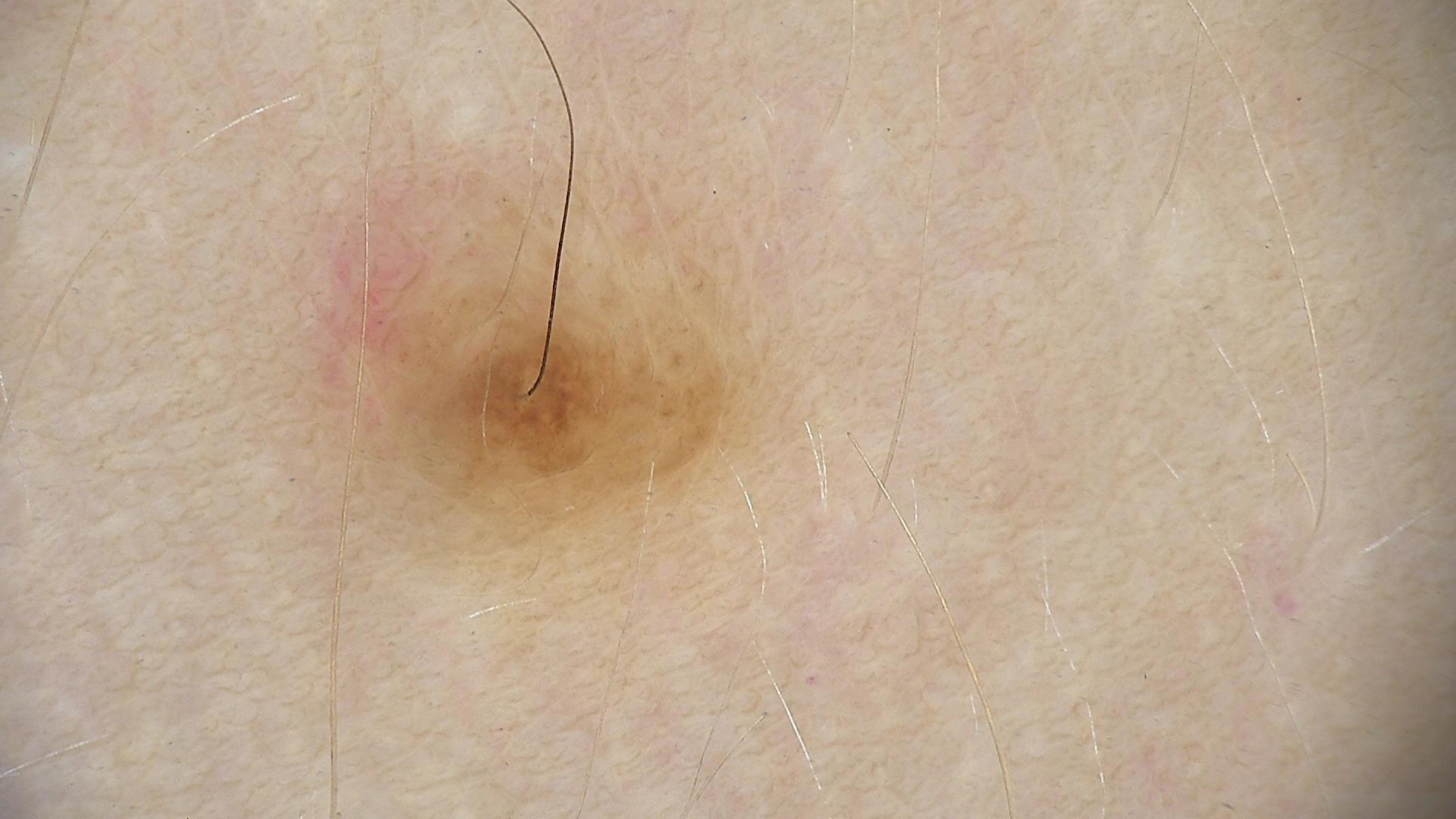diagnosis: dermal nevus (expert consensus).